The photo was captured at a distance · the lesion is associated with bothersome appearance · no constitutional symptoms were reported · the lesion involves the arm — 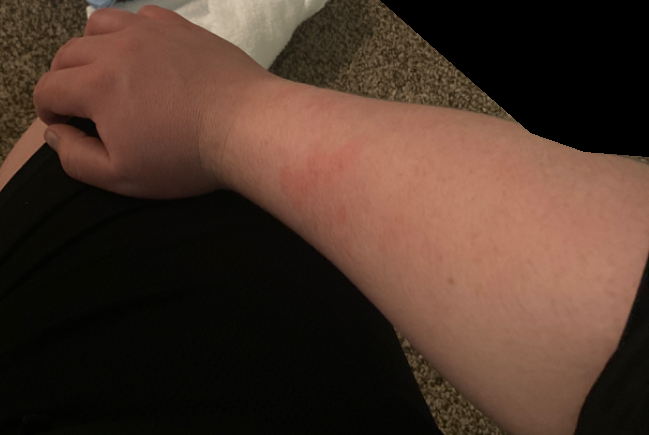Review: The leading consideration is Urticaria.